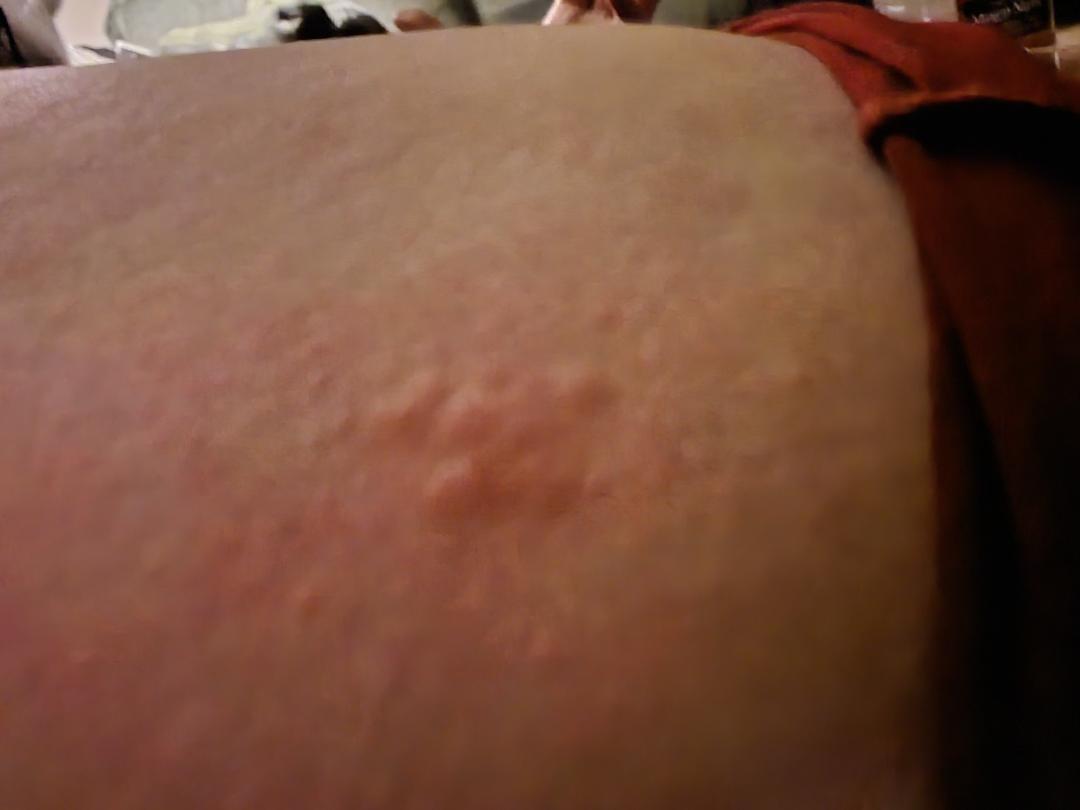{"assessment": "indeterminate from the photograph"}